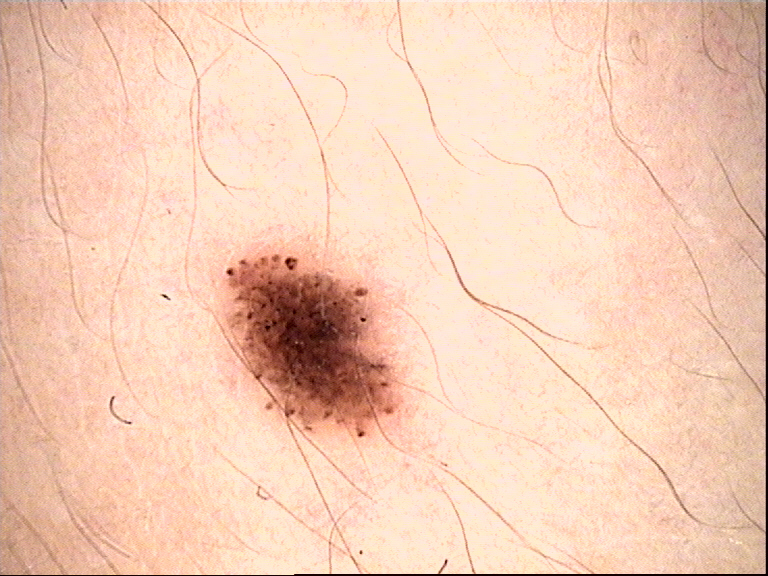Diagnosed as a dysplastic junctional nevus.